Fitzpatrick I; lay reviewers estimated MST 1 or 2, the patient reports the condition has been present for less than one week, the head or neck is involved, texture is reported as fluid-filled, the patient reports pain and itching, self-categorized by the patient as a rash, the photograph is a close-up of the affected area:
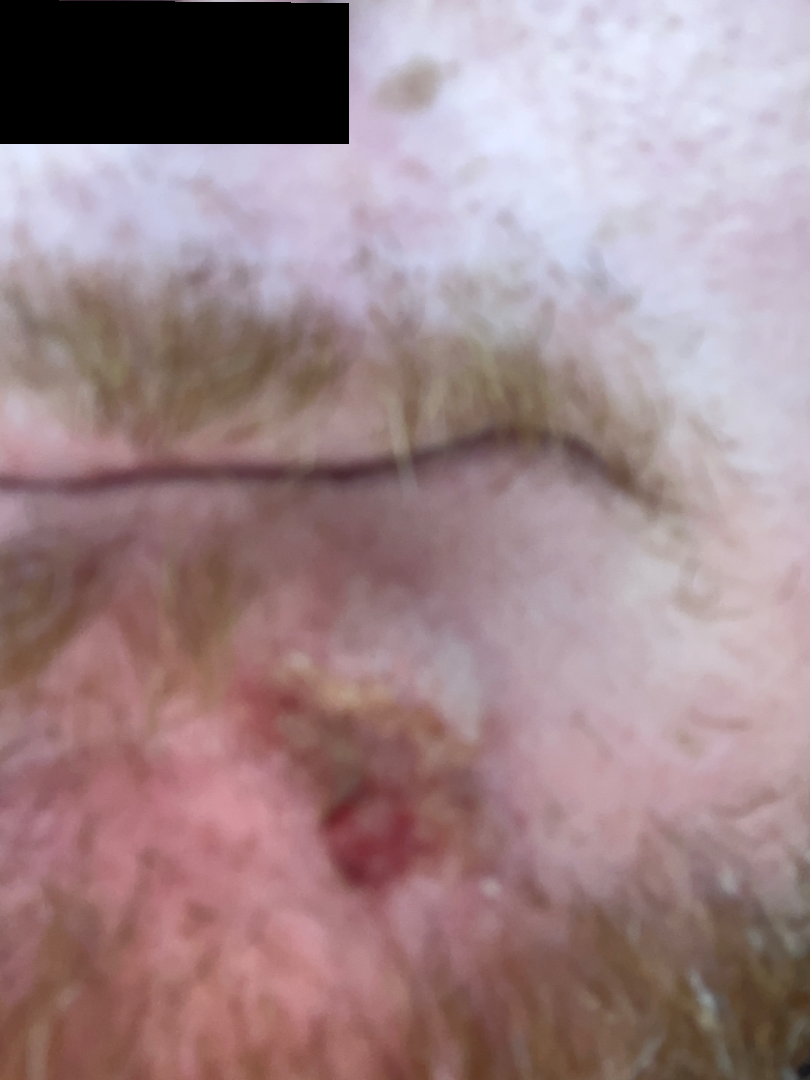  differential: Impetigo